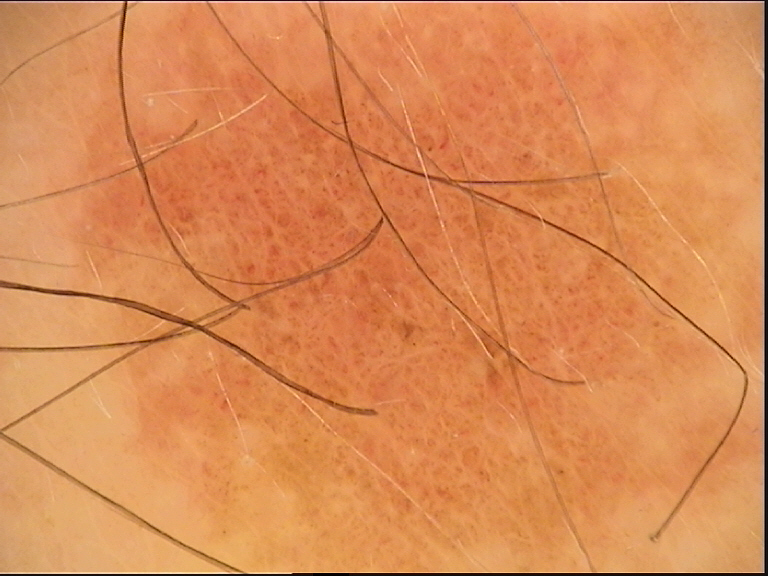Case: A dermoscopic image of a skin lesion. Impression: The diagnosis was a dysplastic junctional nevus.